A dermoscopy image of a single skin lesion.
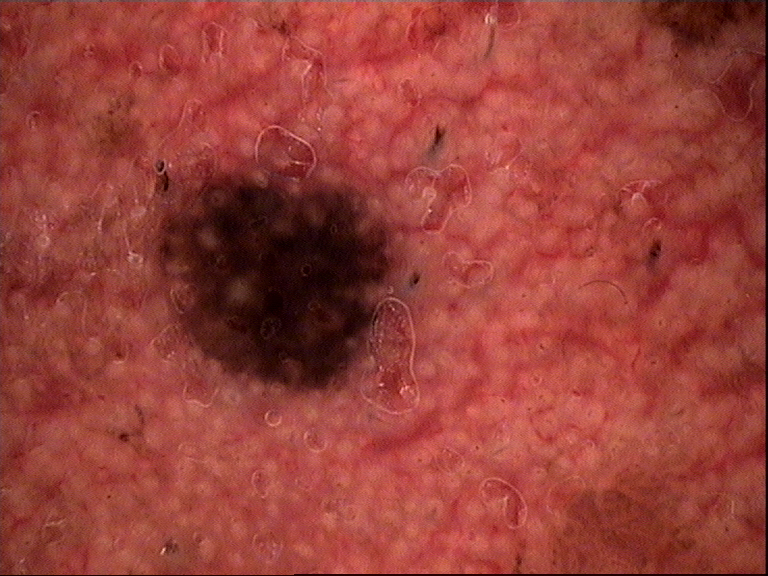Classified as a keratinocytic, benign lesion — a seborrheic keratosis.